The contributor notes the condition has been present for less than one week; located on the arm; skin tone: lay reviewers estimated MST 1 or 2; this image was taken at an angle; the patient considered this a rash:
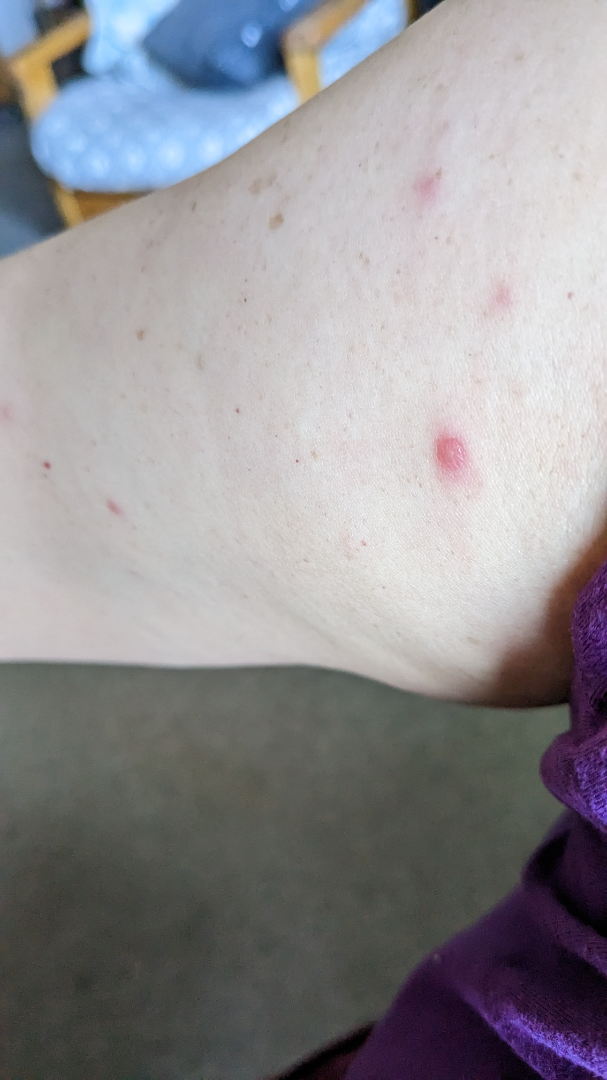assessment: indeterminate.